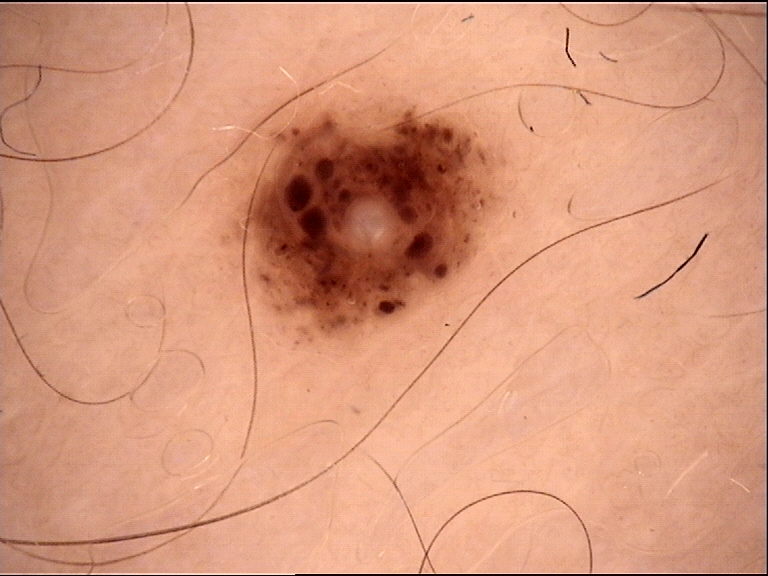  image: dermatoscopy
  diagnosis:
    name: dysplastic junctional nevus
    code: jd
    malignancy: benign
    super_class: melanocytic
    confirmation: expert consensus